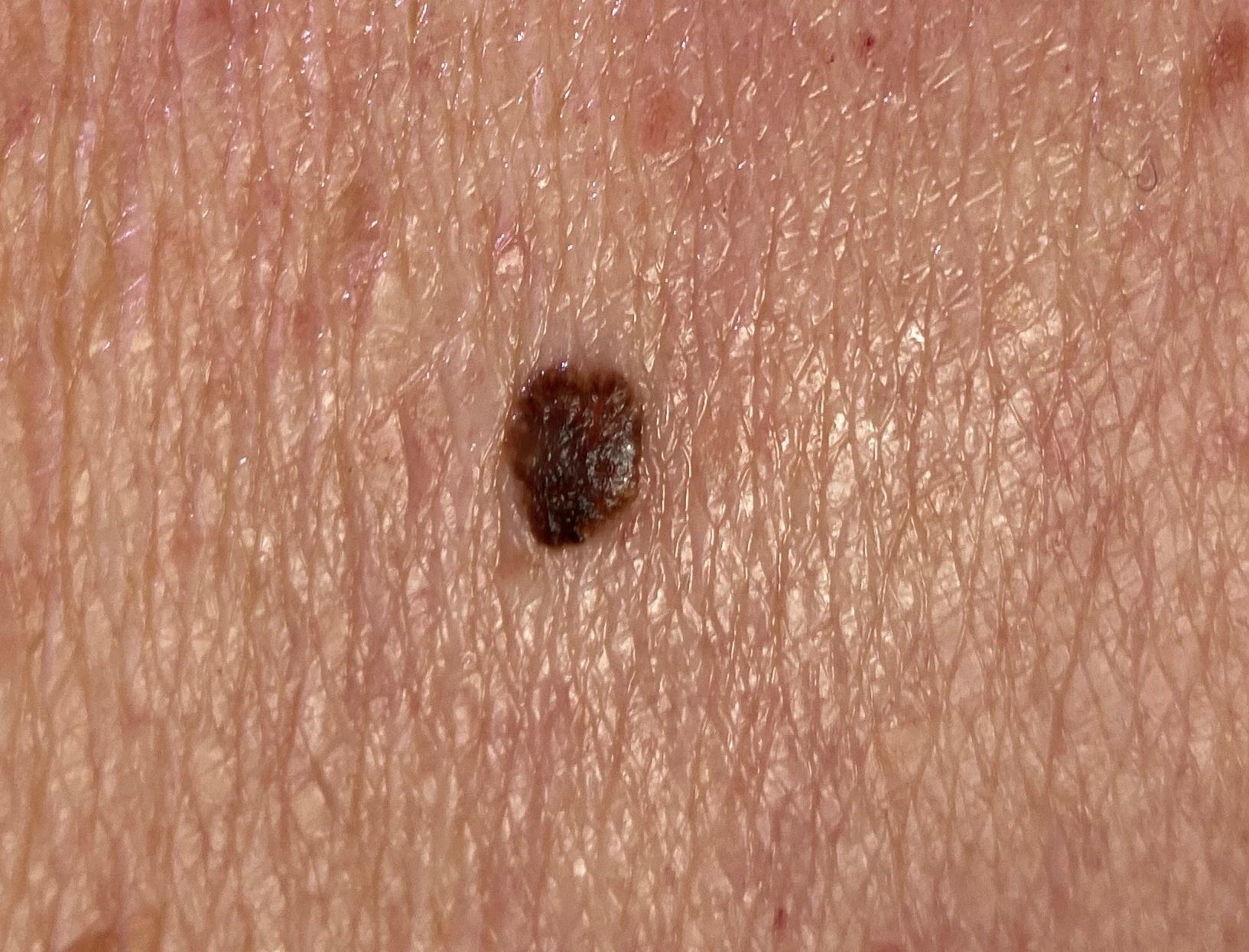Case summary: A male patient aged 83 or older. A clinical overview photograph of a skin lesion. The lesion is located on the trunk (the anterior trunk). Diagnosis: Histopathological examination showed a seborrheic keratosis.